The contributor notes burning. The lesion is described as raised or bumpy. Present for about one day. Located on the leg. No constitutional symptoms were reported. The patient considered this a rash. A close-up photograph — 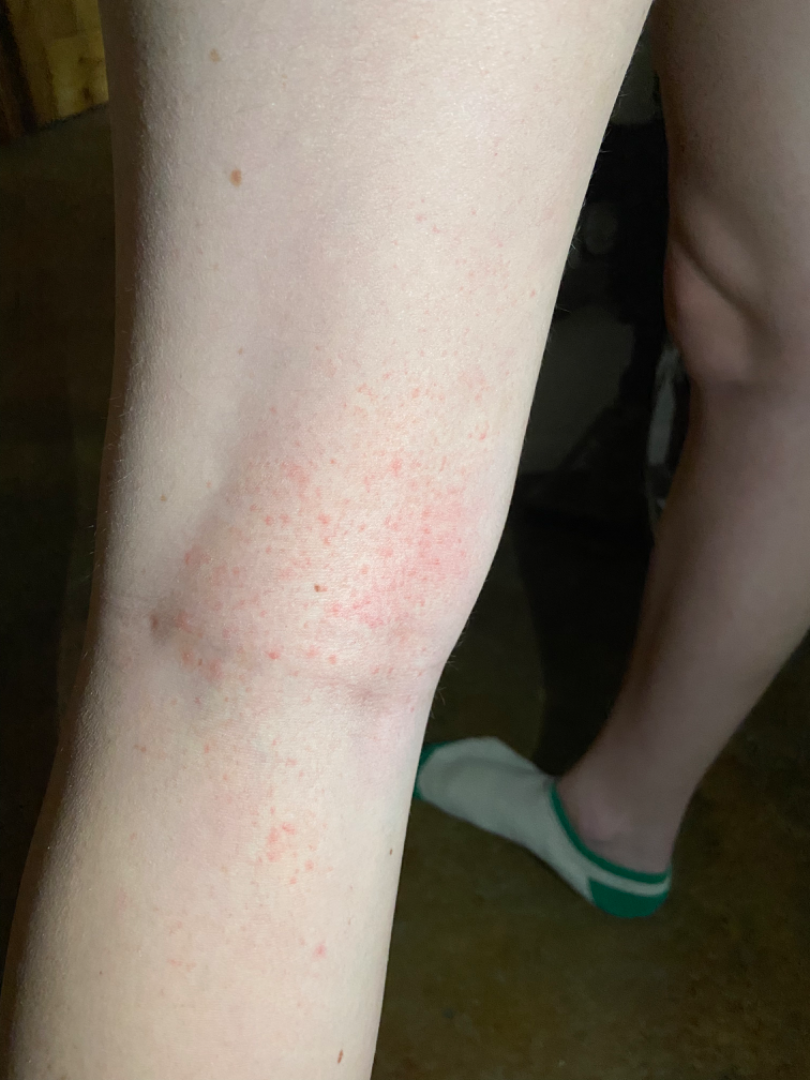Assessment:
Most consistent with Eczema.